A dermoscopic close-up of a skin lesion.
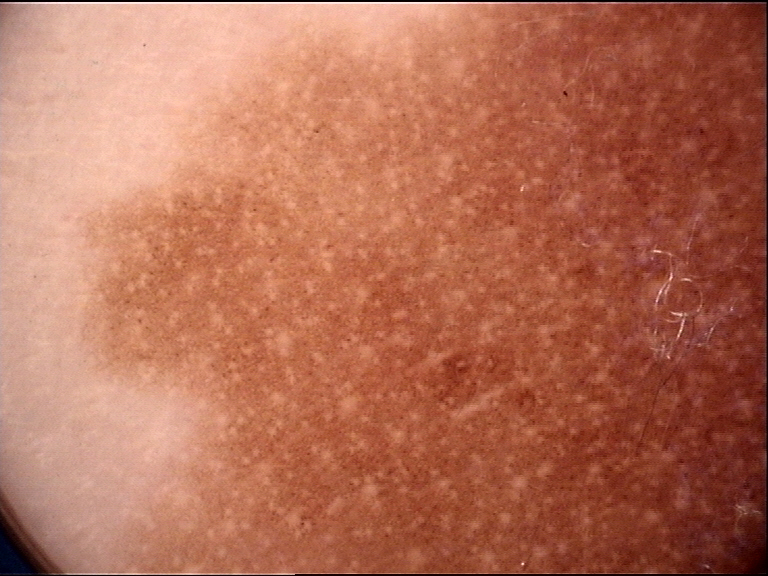{
  "diagnosis": {
    "name": "congenital compound nevus",
    "code": "ccb",
    "malignancy": "benign",
    "super_class": "melanocytic",
    "confirmation": "expert consensus"
  }
}